Close-up view: 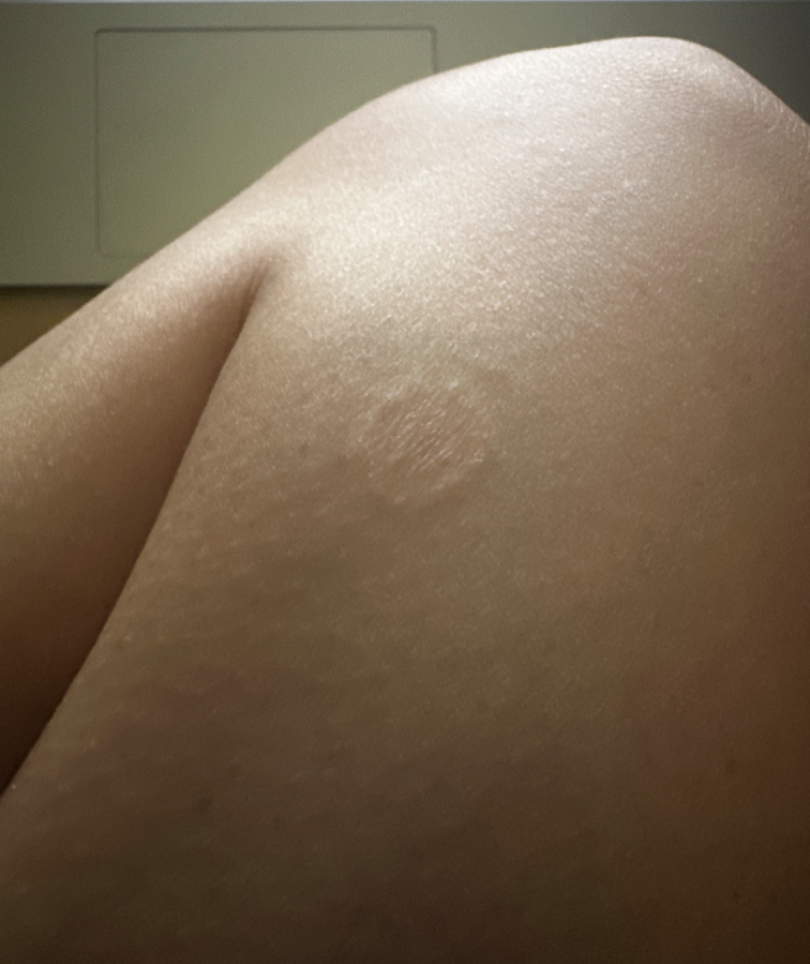On remote review of the image, Tinea, Eczema and Psoriasis were considered with similar weight.